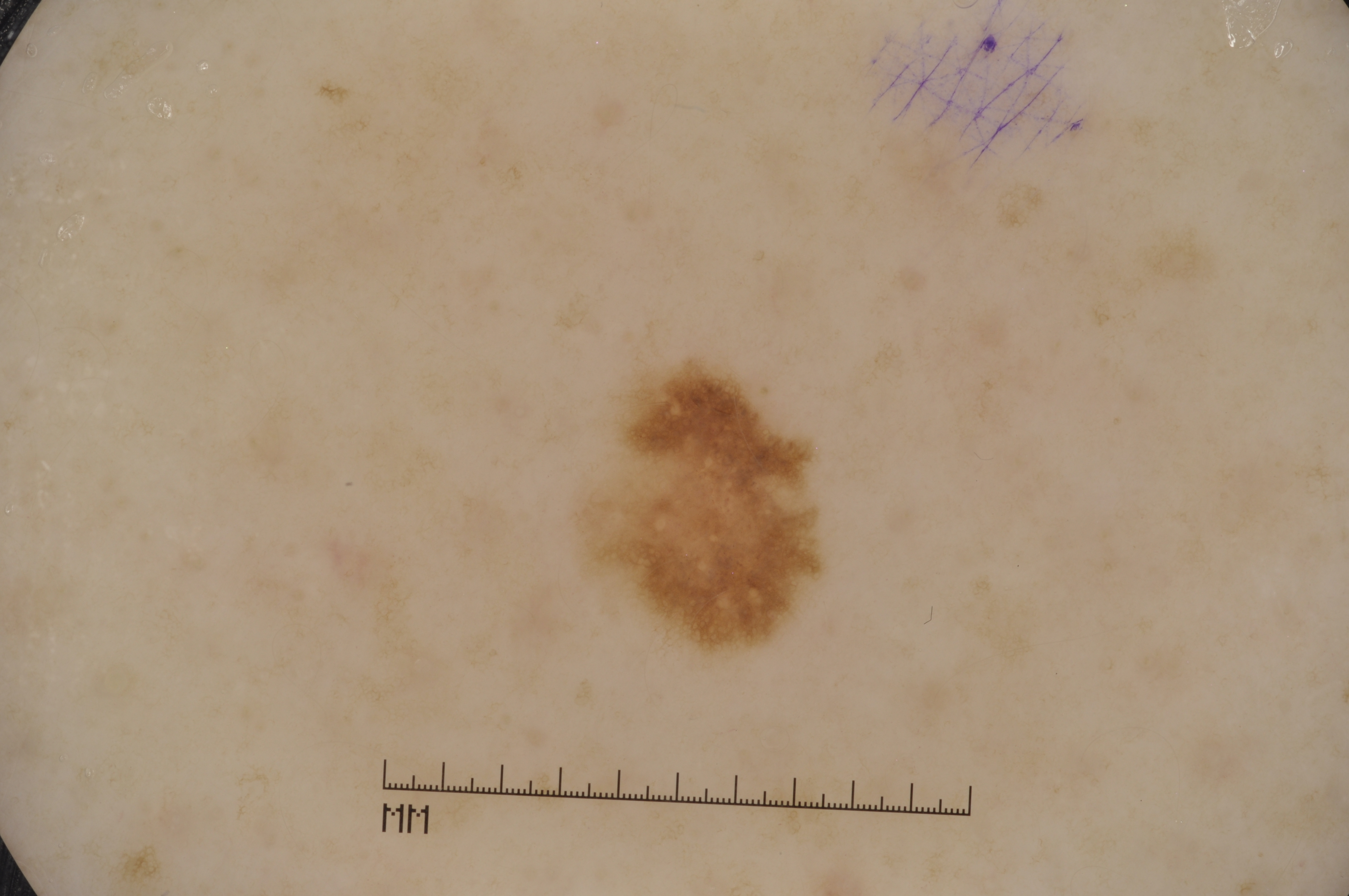Summary: A female subject, aged 43-47. A dermoscopic view of a skin lesion. In (x1, y1, x2, y2) order, the lesion's extent is [554,312,838,677]. Dermoscopic review identifies pigment network, with no milia-like cysts, negative network, or streaks. Conclusion: The diagnostic assessment was a melanocytic nevus.